A dermoscopic image of a skin lesion.
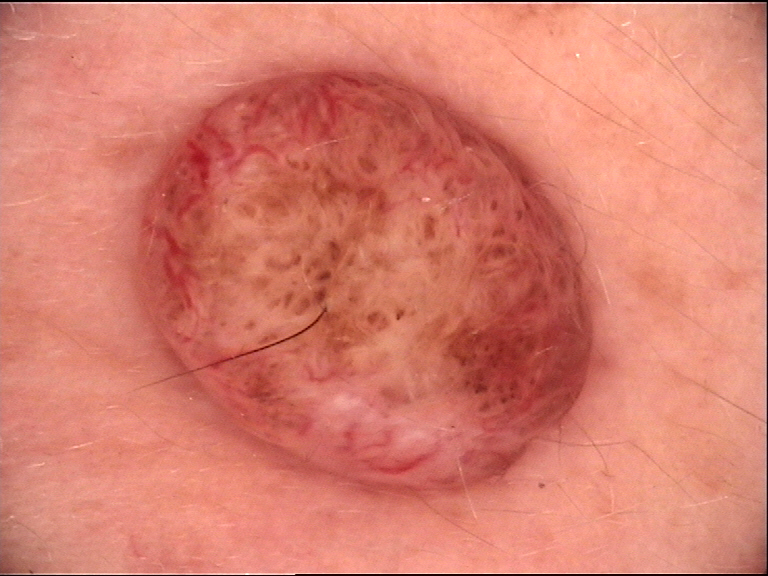This is a banal lesion. Consistent with a dermal nevus.